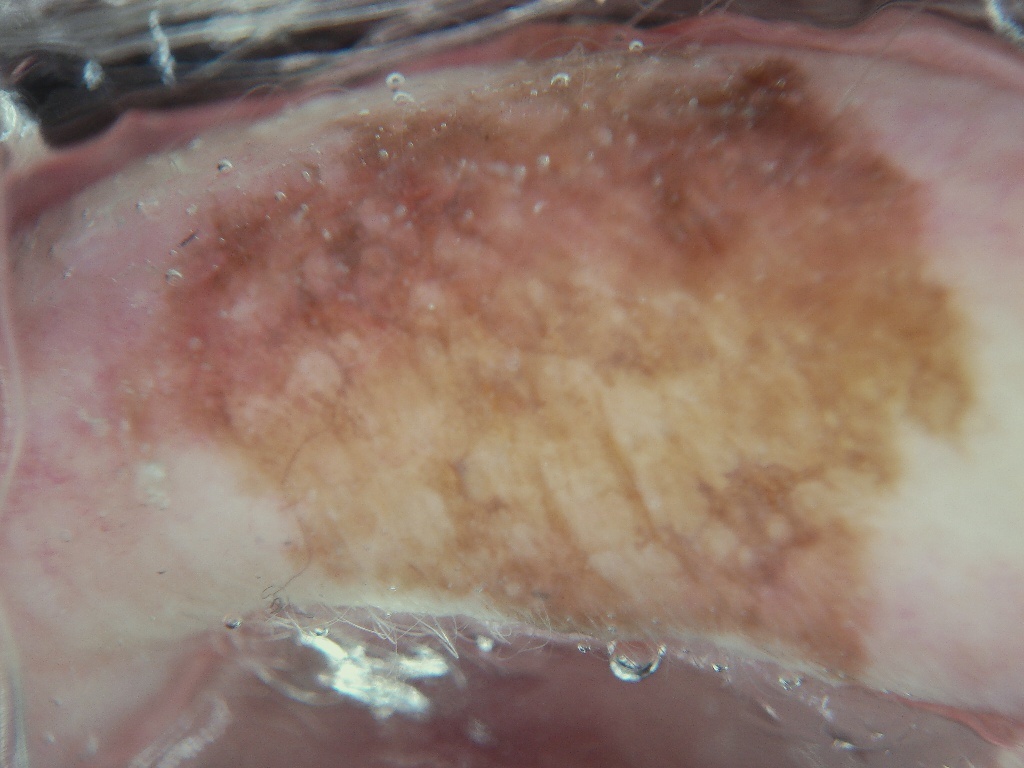modality = dermoscopy of a skin lesion; lesion location = box(106, 43, 993, 682); extent = large; diagnosis = a benign lesion.